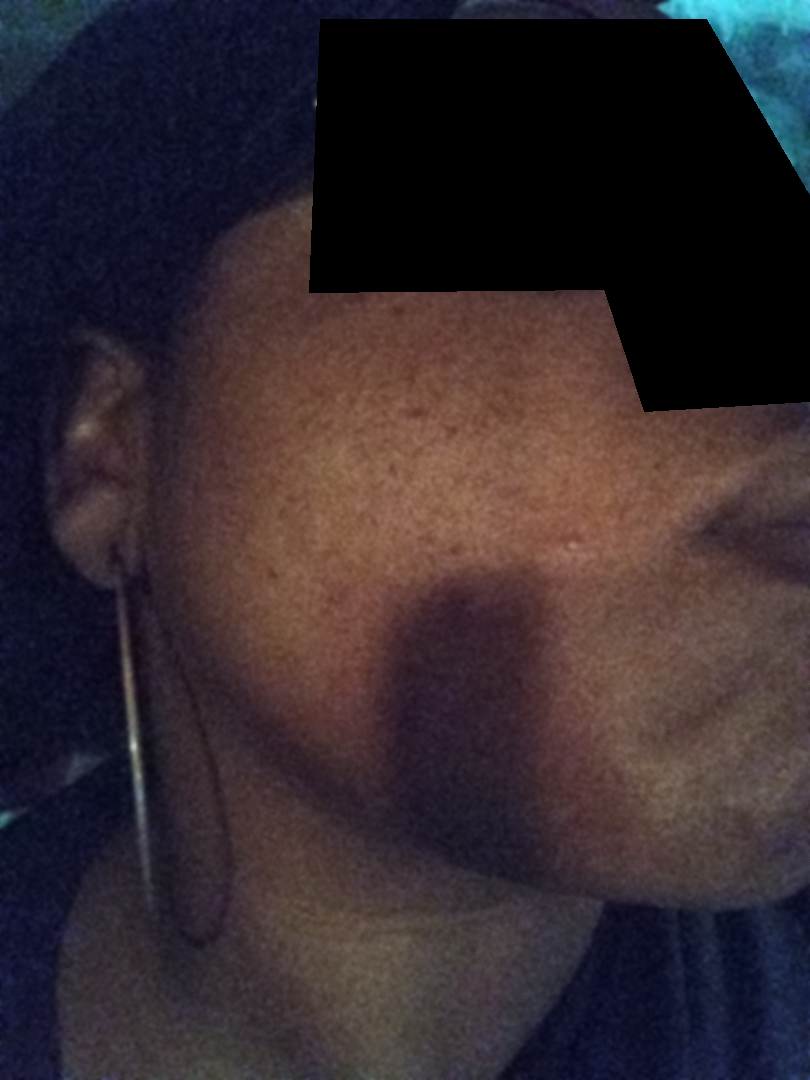The case was indeterminate on photographic review. An image taken at an angle.